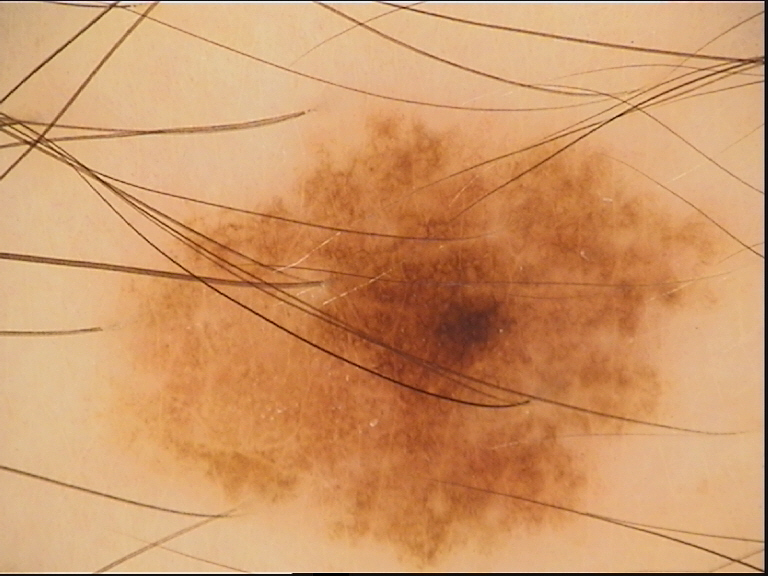A dermoscopy image of a single skin lesion. Consistent with a dysplastic junctional nevus.